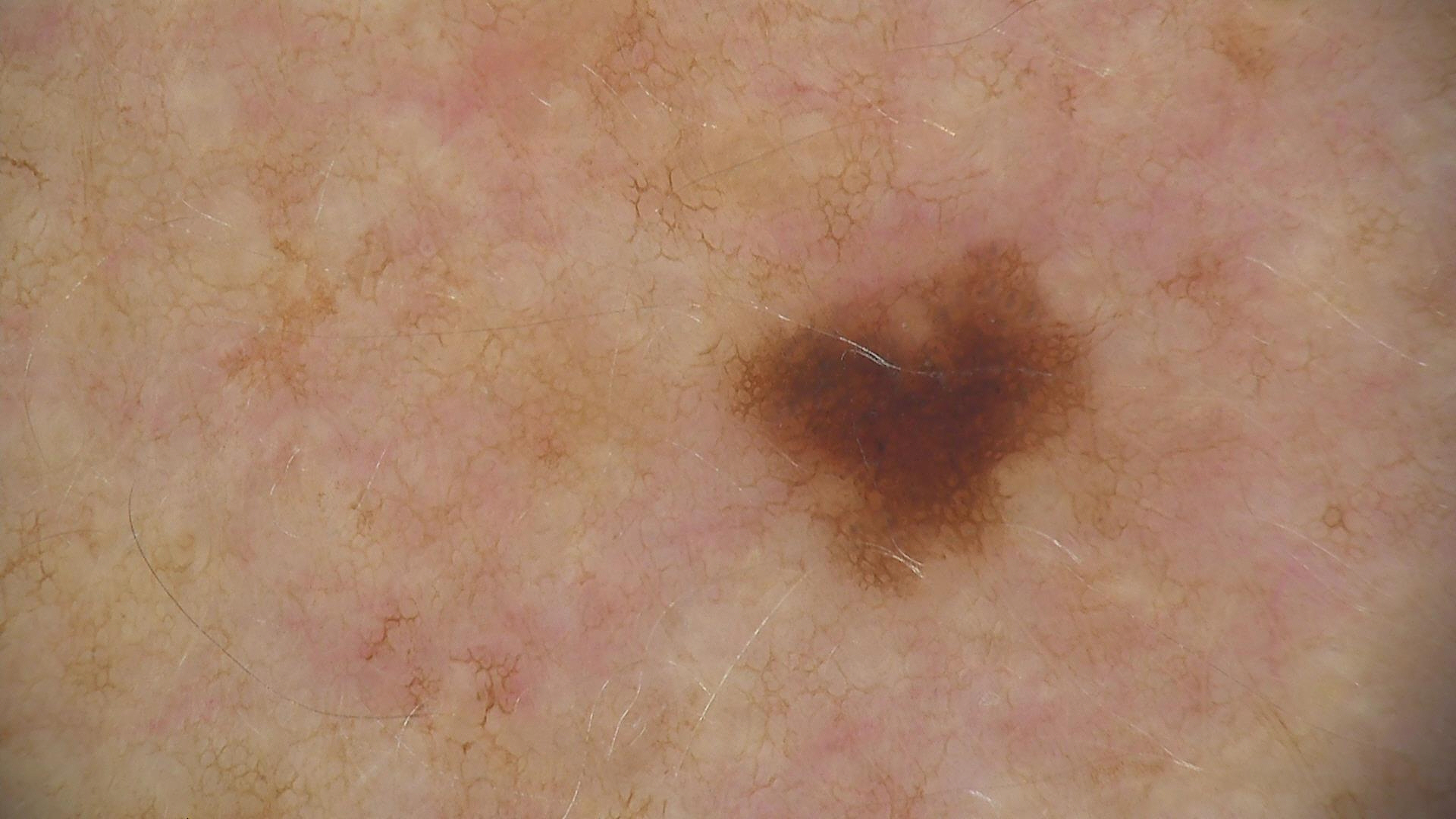class = dysplastic junctional nevus (expert consensus).